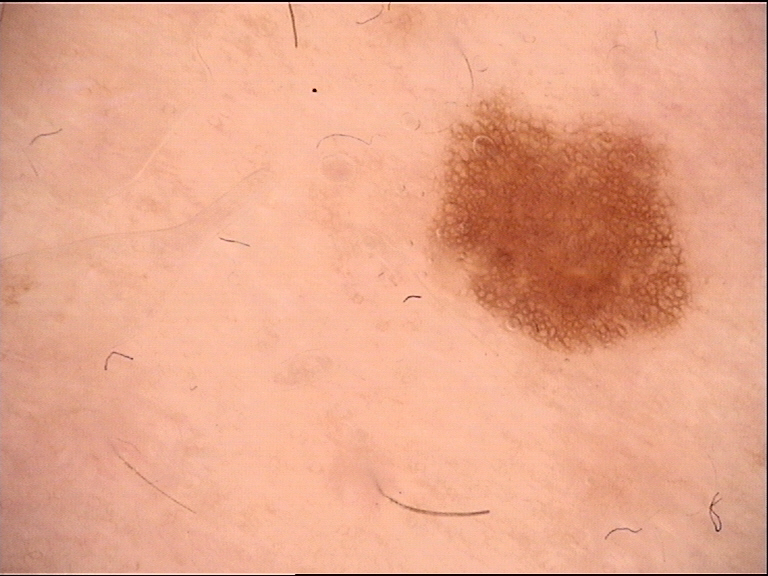Case:
• image type — dermatoscopy
• assessment — dysplastic junctional nevus (expert consensus)